A skin lesion imaged with a dermatoscope:
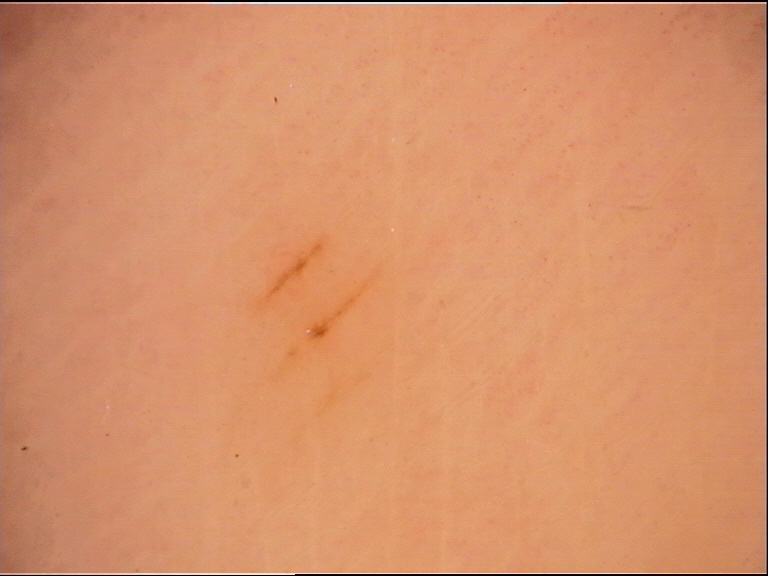diagnostic label = acral junctional nevus (expert consensus)